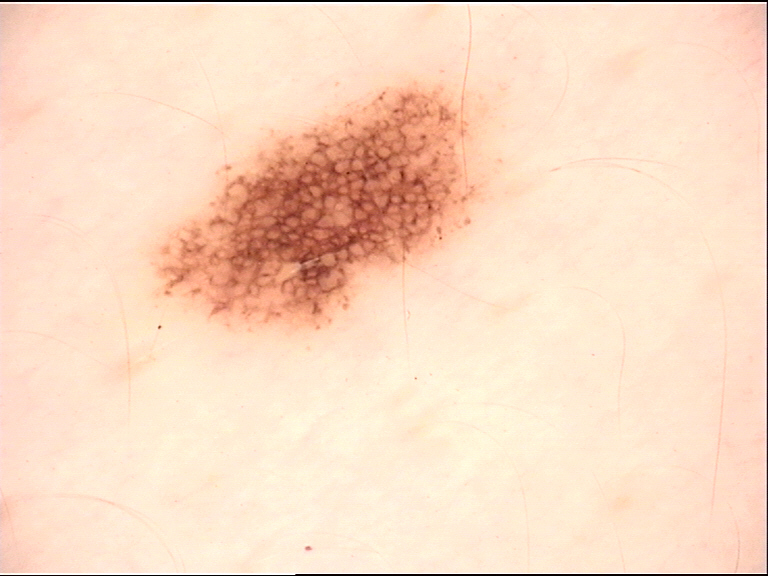label = junctional nevus (expert consensus).